The photograph is a close-up of the affected area — 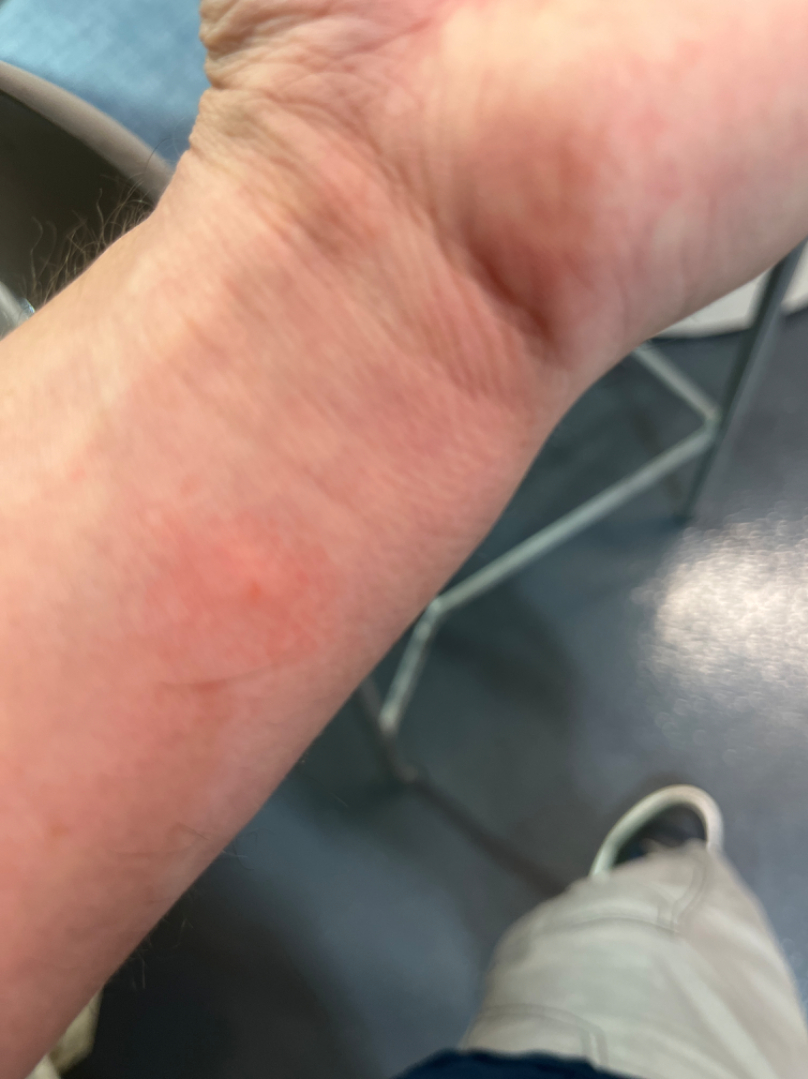Findings:
- assessment · could not be assessed